The affected area is the arm, the photo was captured at an angle — 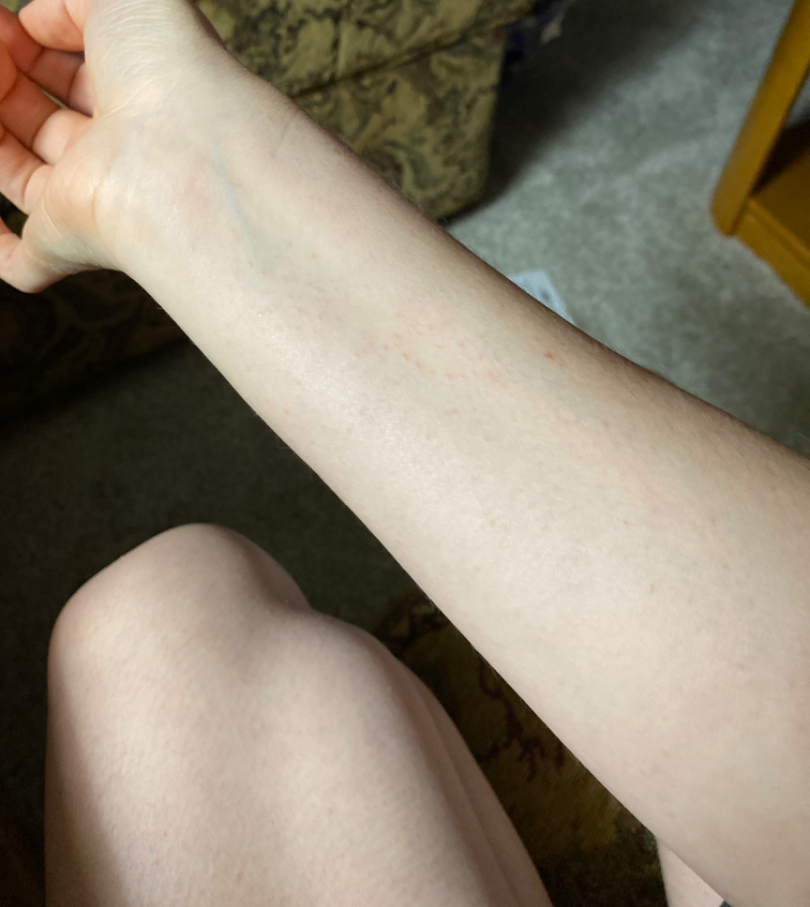Impression: The skin condition could not be confidently assessed from this image. History: The patient considered this skin that appeared healthy to them. Texture is reported as raised or bumpy. The patient reports bothersome appearance. Reported duration is about one day.